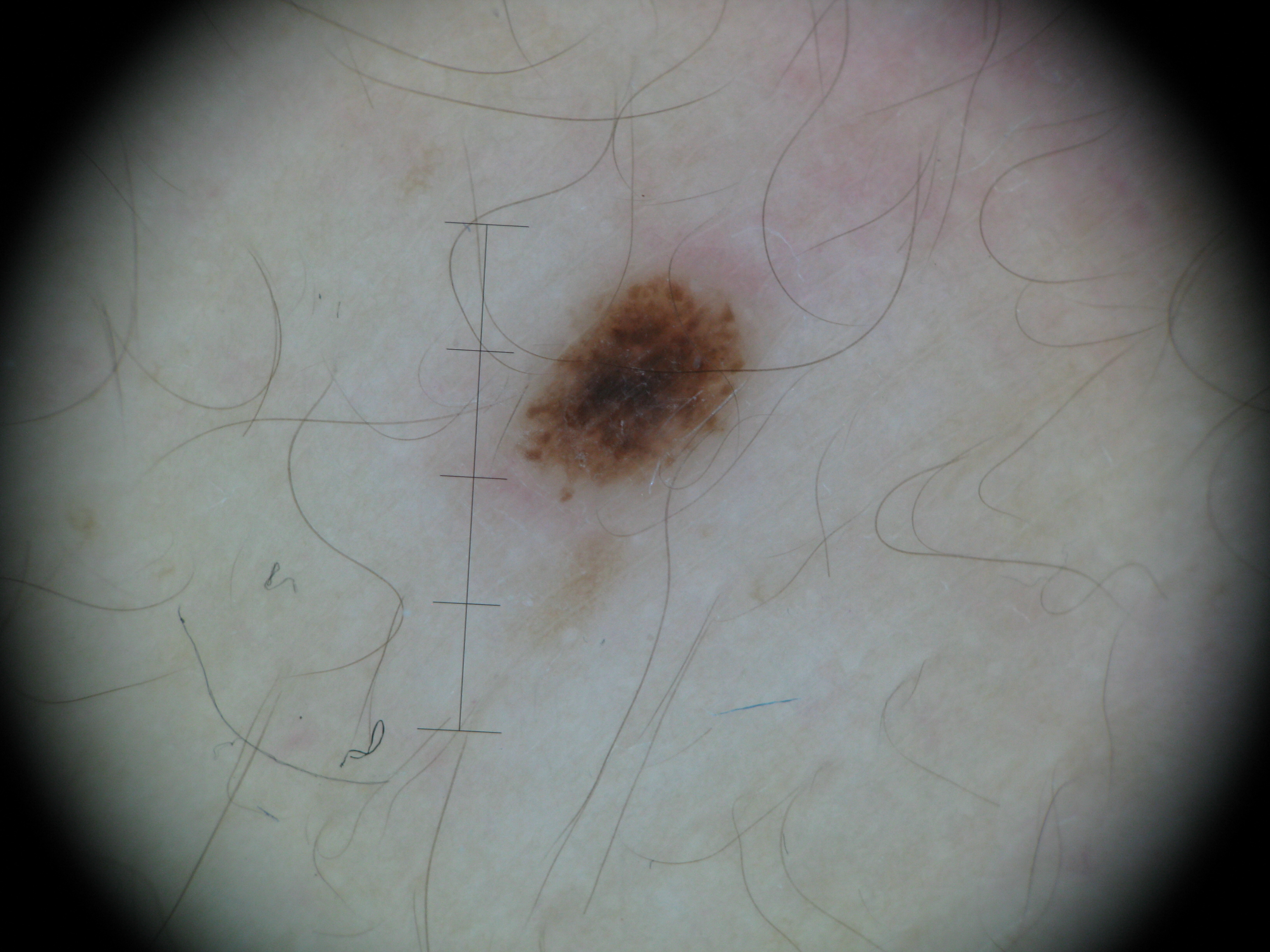Findings:
A dermoscopic photograph of a skin lesion.
Impression:
Diagnosed as a dysplastic junctional nevus.